Dermoscopy of a skin lesion.
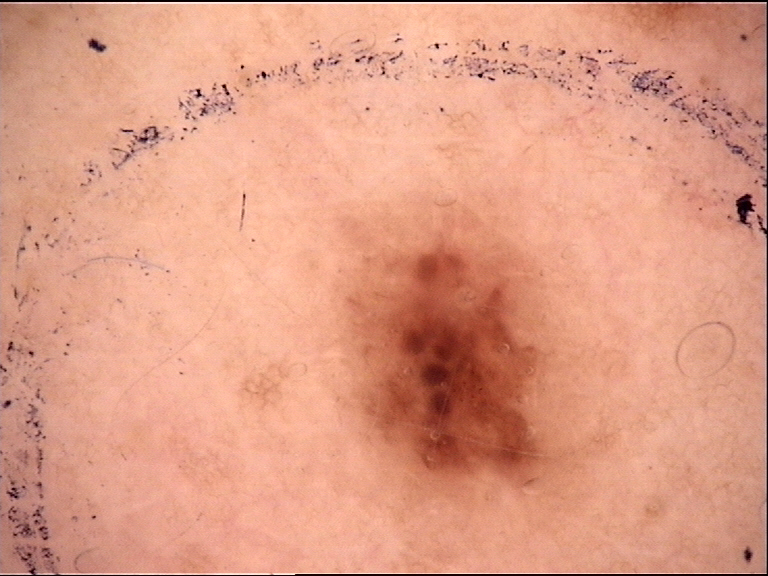Findings:
• assessment · dysplastic junctional nevus (expert consensus)